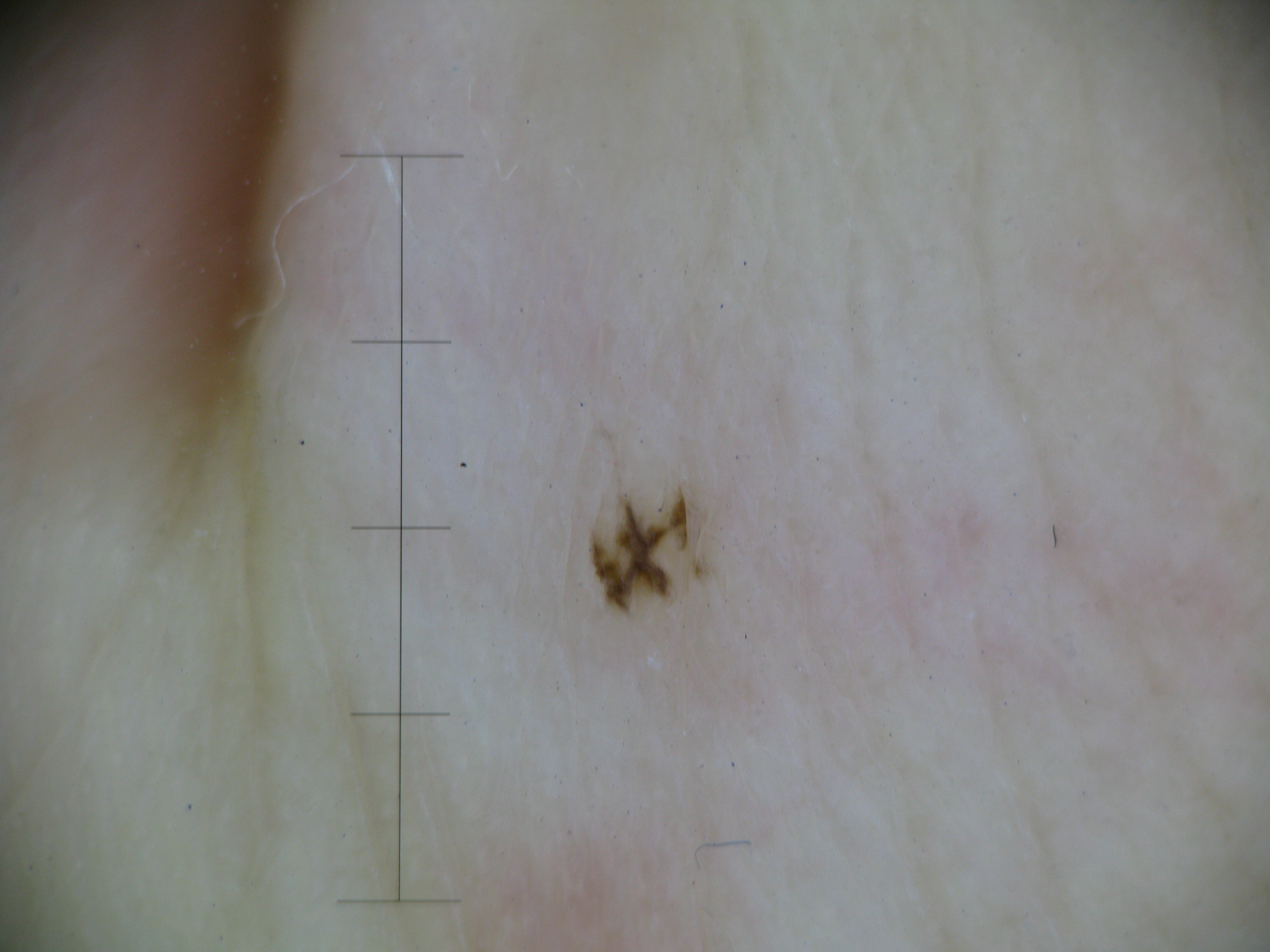The diagnosis was a banal lesion — an acral junctional nevus.